A skin lesion imaged with a dermatoscope: 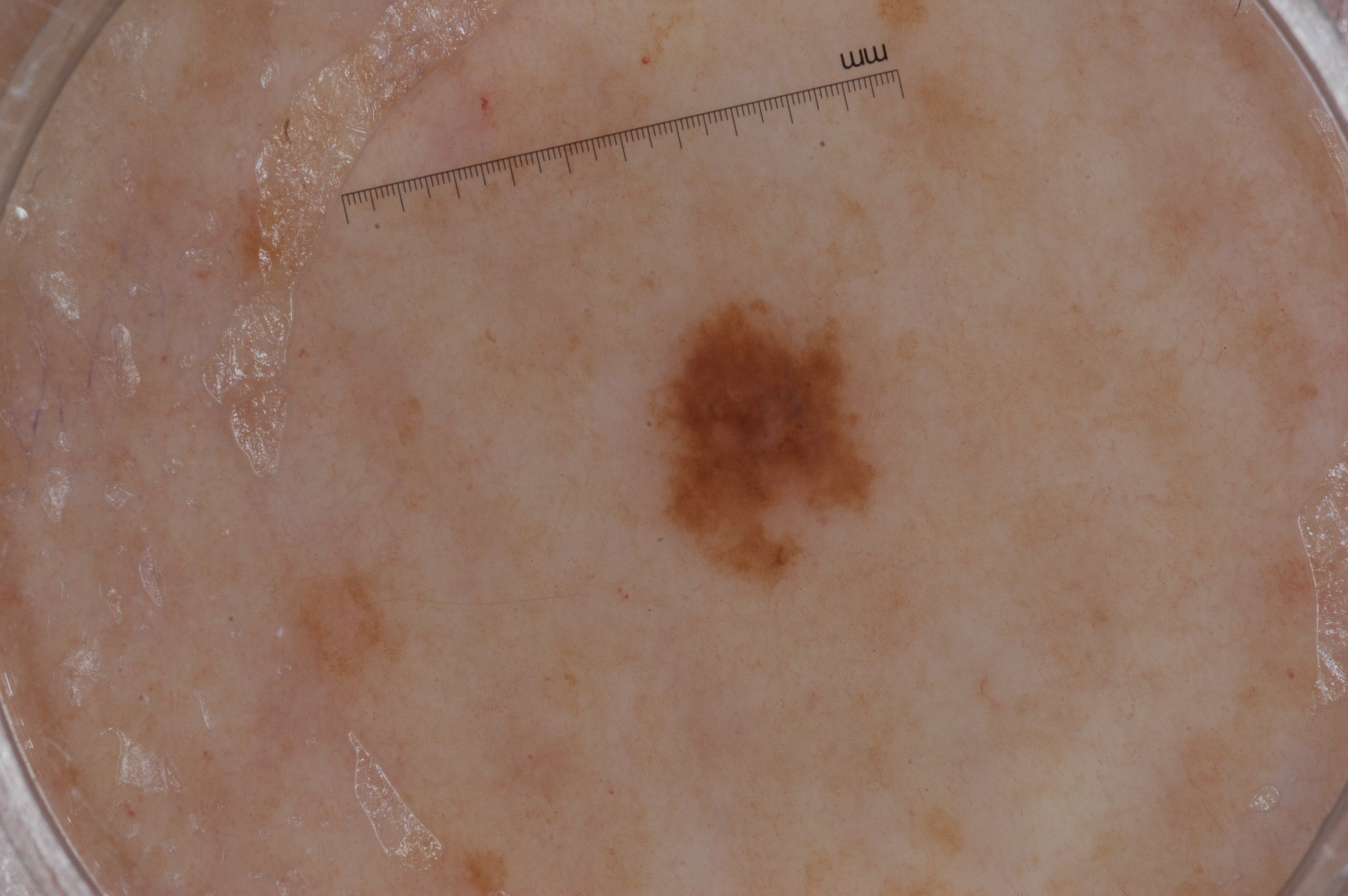Q: Where is the lesion located?
A: bbox(653, 301, 874, 574)
Q: What is this lesion?
A: a melanocytic nevus, a benign lesion